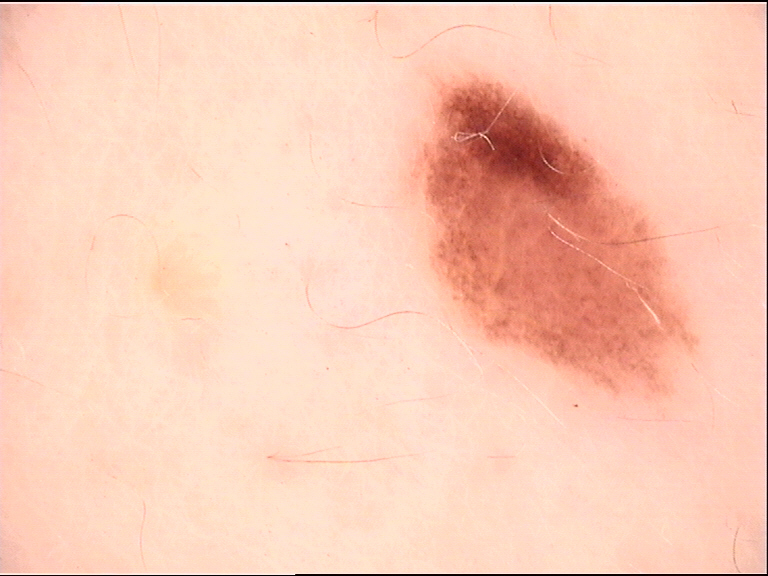Conclusion:
The diagnosis was a dysplastic junctional nevus.